A dermoscopic close-up of a skin lesion:
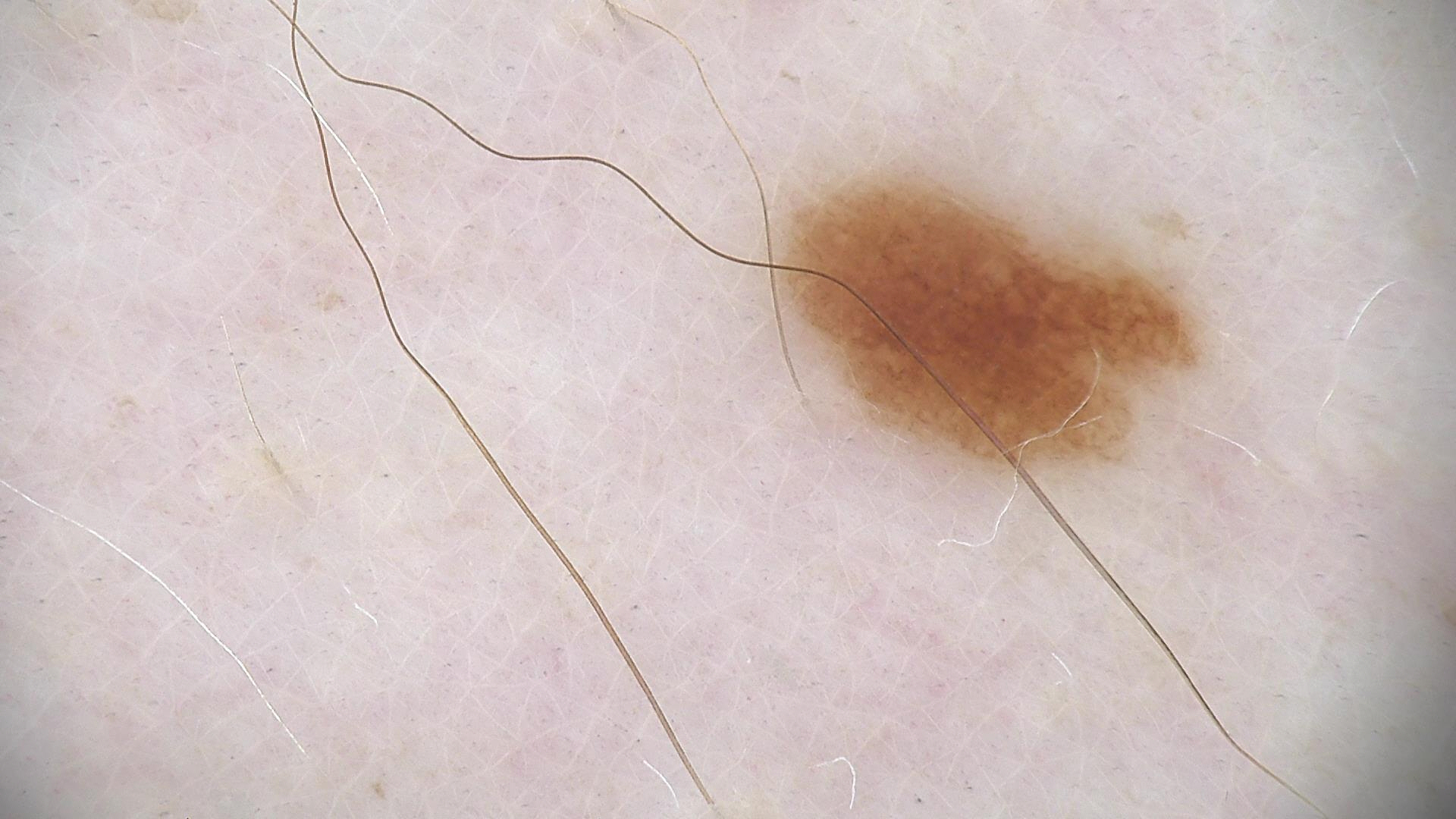The diagnostic label was a benign lesion — a dysplastic junctional nevus.